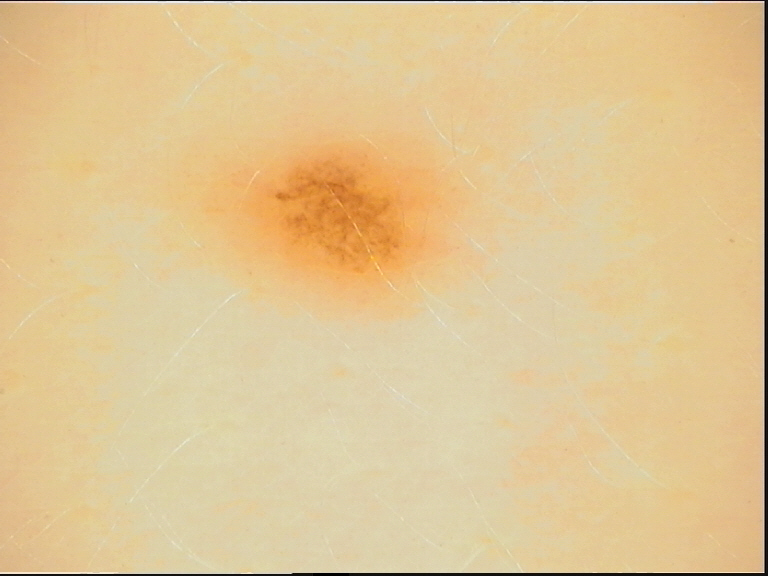Labeled as a banal lesion — a junctional nevus.